Dermoscopy of a skin lesion.
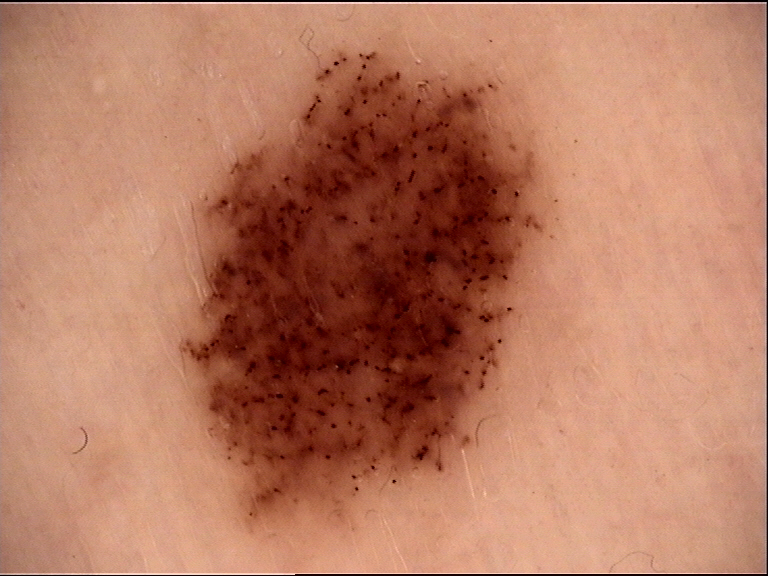Q: What was the diagnostic impression?
A: dysplastic junctional nevus (expert consensus)